The lesion involves the leg and arm, skin tone: Fitzpatrick II, texture is reported as raised or bumpy, the photograph is a close-up of the affected area:
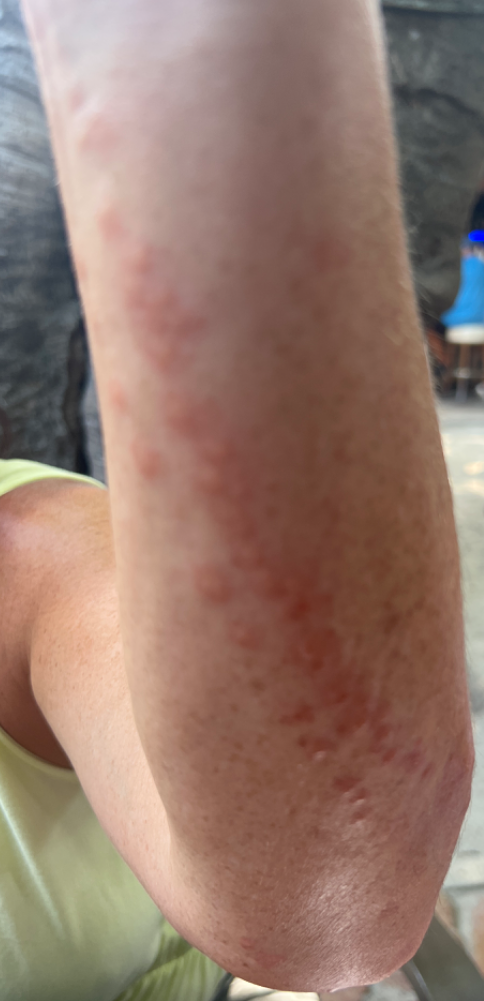The case was difficult to assess from the available photograph.